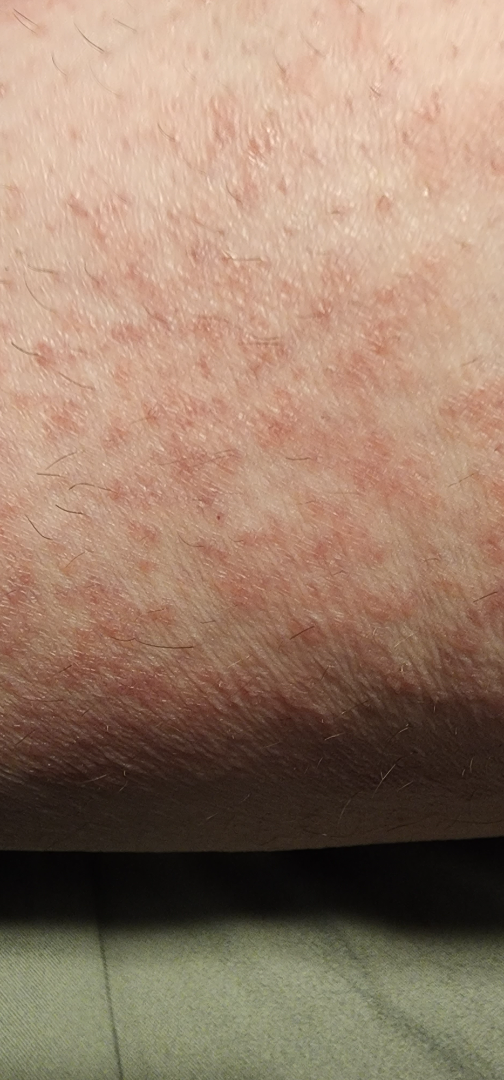The photograph is a close-up of the affected area.
The patient is a female aged 40–49.
The leg is involved.
Viral Exanthem (possible); Drug Rash (possible); Allergic Contact Dermatitis (unlikely).